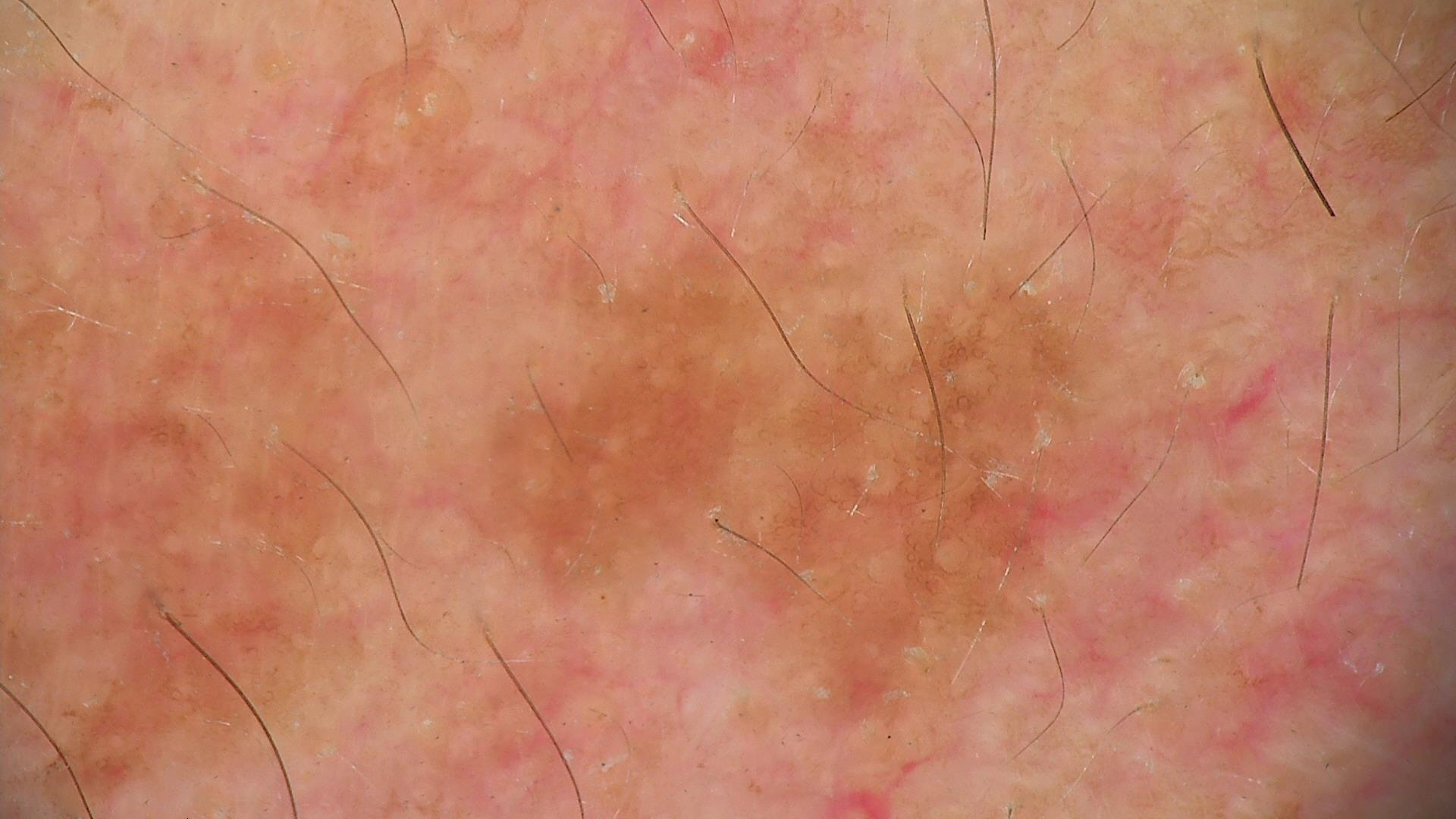modality: dermatoscopy; diagnosis: seborrheic keratosis (expert consensus).